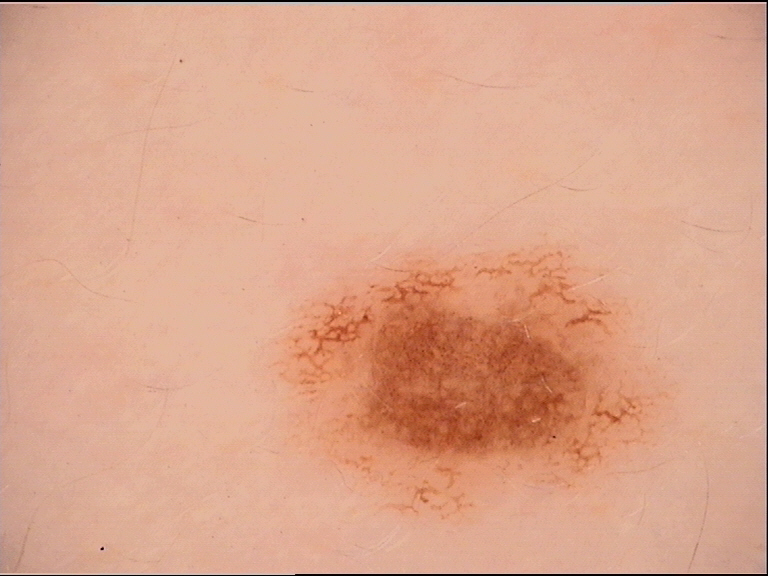diagnosis: dysplastic junctional nevus (expert consensus).